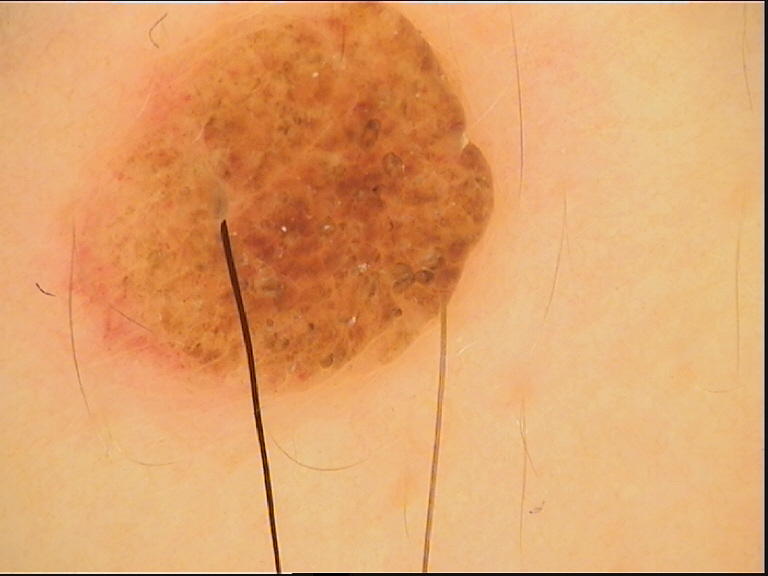This is a banal lesion.
Labeled as a compound nevus.